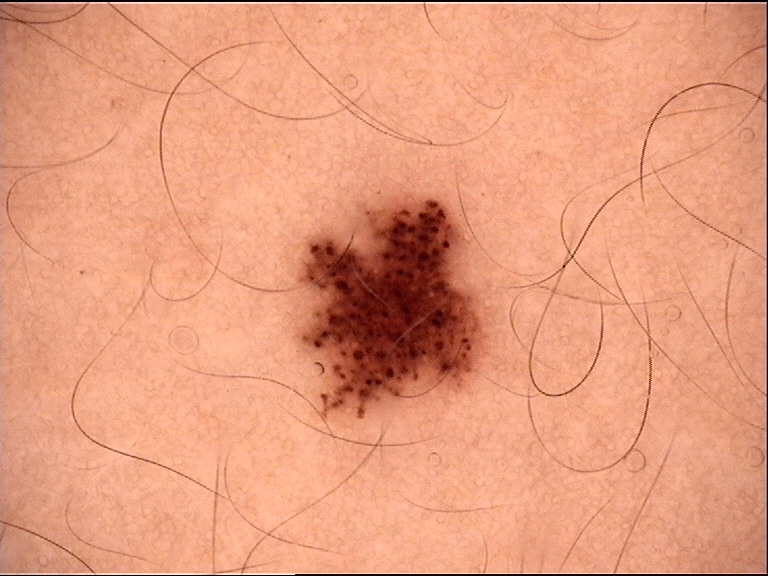Diagnosed as a compound nevus.